A wide-field clinical photograph of a skin lesion. A female subject approximately 40 years of age.
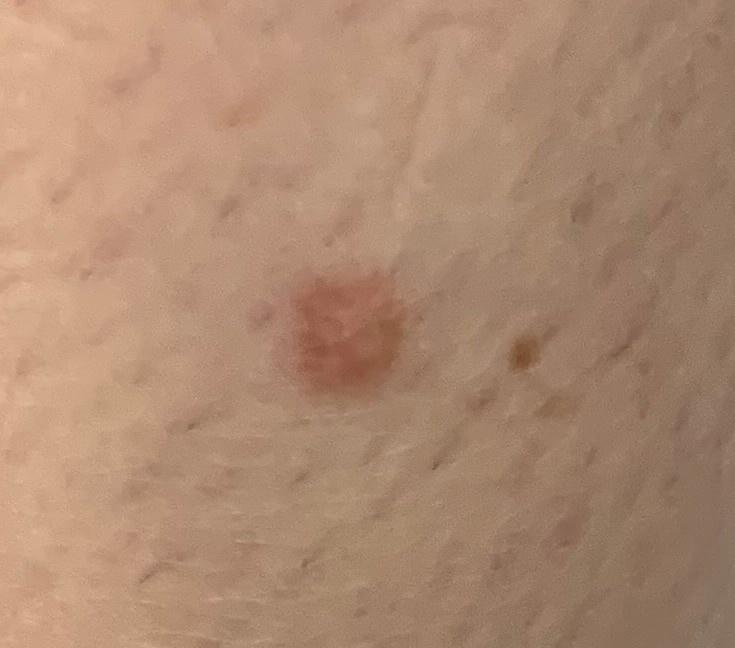location: a lower extremity; impression: Dermatofibroma.